The affected area is the leg. This image was taken at an angle — 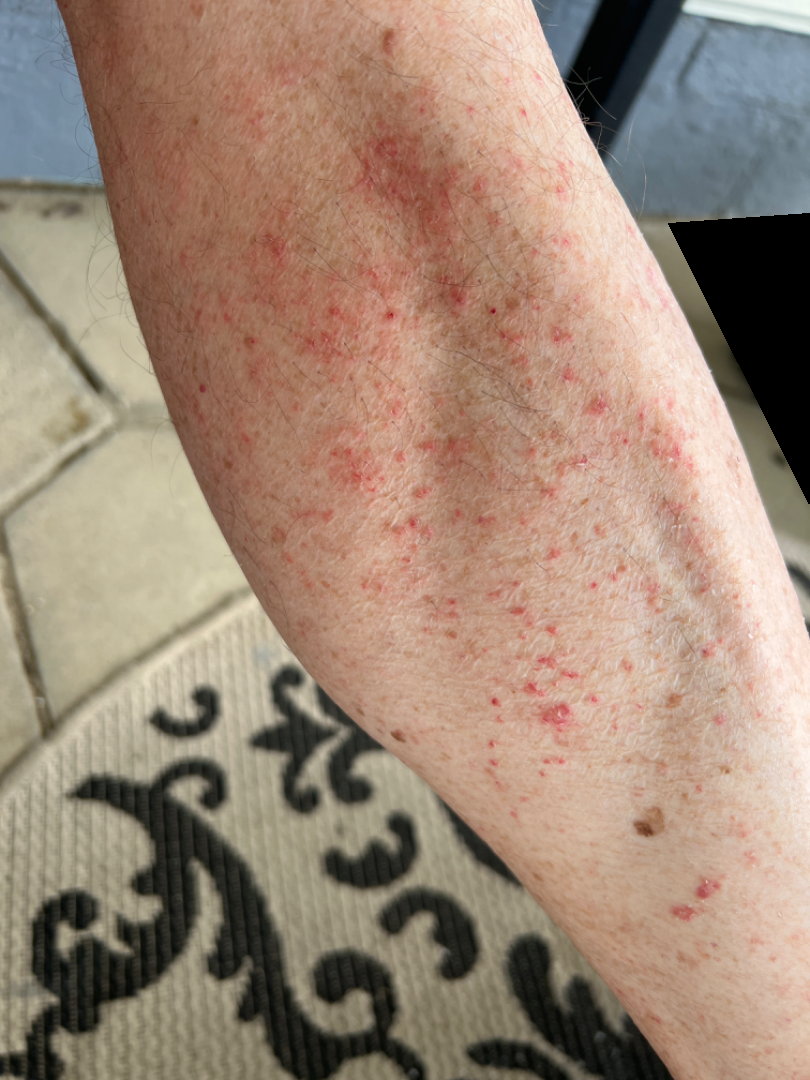dermatologist impression: consistent with Acute dermatitis, NOS.